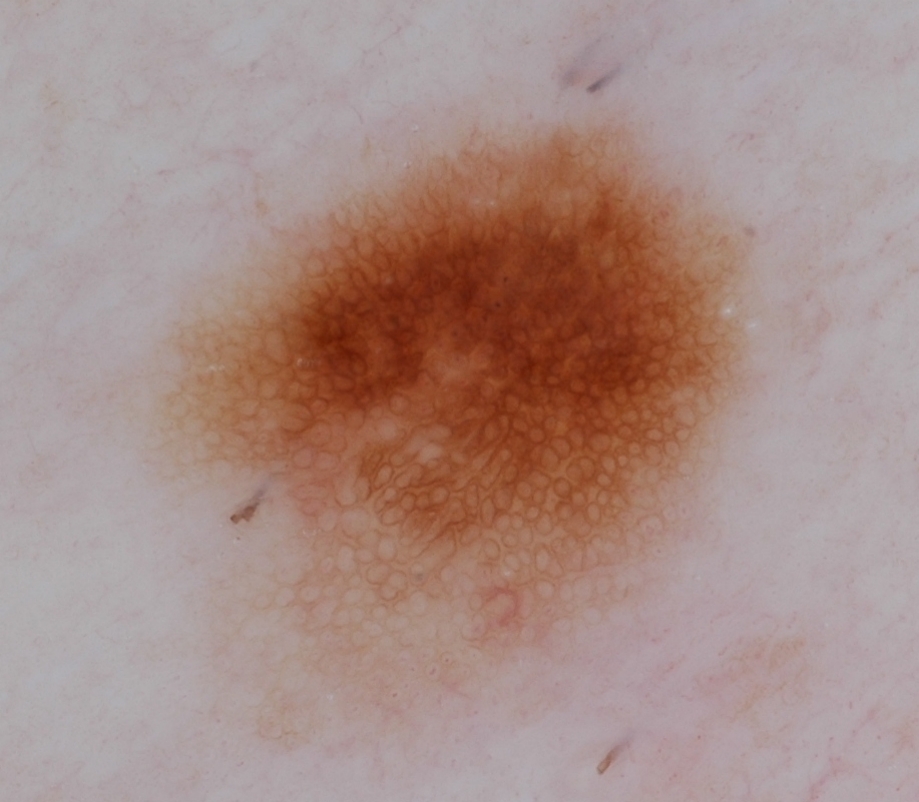imaging=dermoscopy of a skin lesion
features=pigment network and globules; absent: milia-like cysts, negative network, and streaks
lesion bbox=[133, 92, 776, 772]
lesion size=~45% of the field
diagnostic label=a melanocytic nevus